A dermoscopic close-up of a skin lesion: 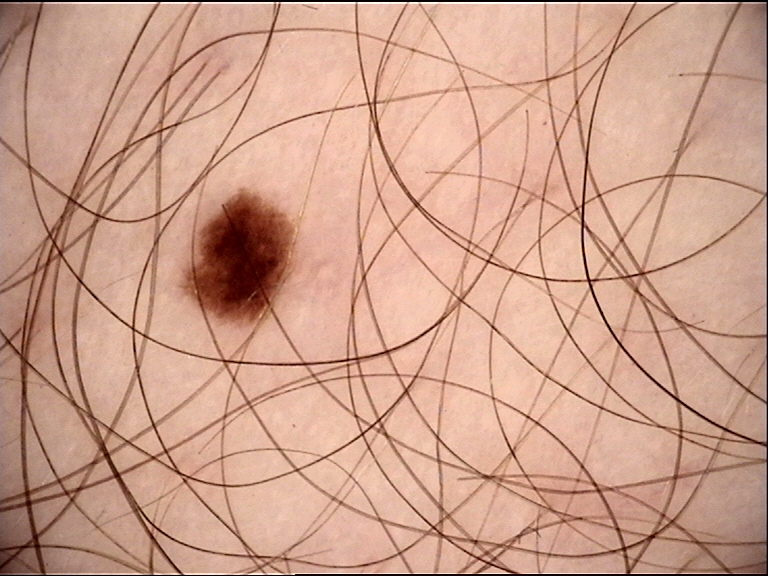Findings:
This is a banal lesion.
Impression:
The diagnostic label was a junctional nevus.